Located on the front of the torso and arm · the subject is a female aged 18–29 · the lesion is associated with itching, pain and burning · the patient described the issue as a rash · the patient indicates the condition has been present for less than one week · this image was taken at an angle:
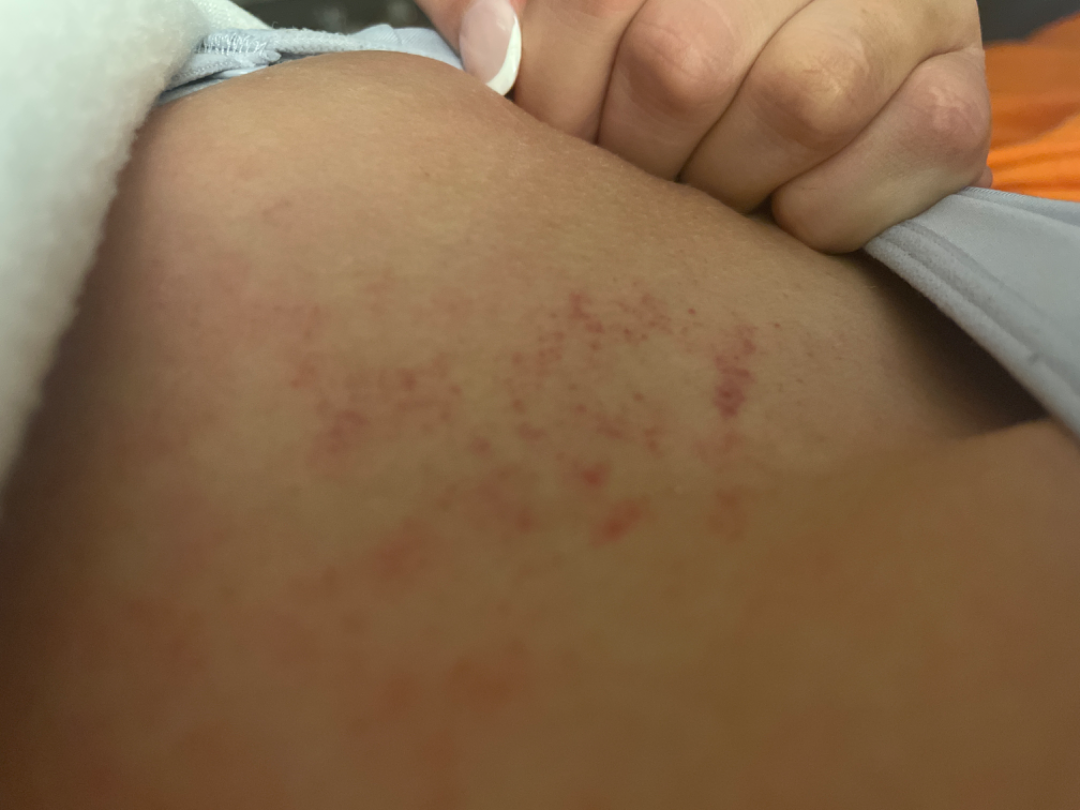The reviewing dermatologists' impression was: Eczema (weight 0.44); Traumatic petechiae (weight 0.17); Allergic Contact Dermatitis (weight 0.17); Viral Exanthem (weight 0.11); Leukocytoclastic Vasculitis (weight 0.11).